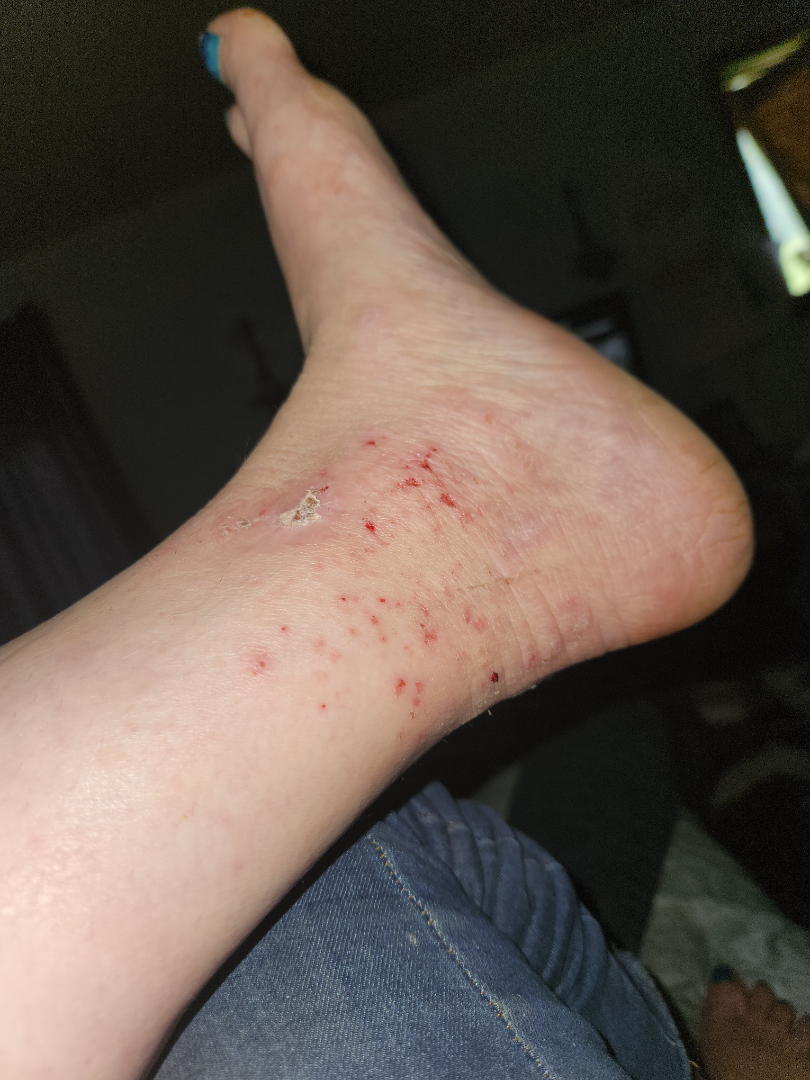The skin findings could not be characterized from the image.